The affected area is the front of the torso, arm, head or neck, back of the torso and leg; the photograph was taken at a distance; the patient is 18–29, female:
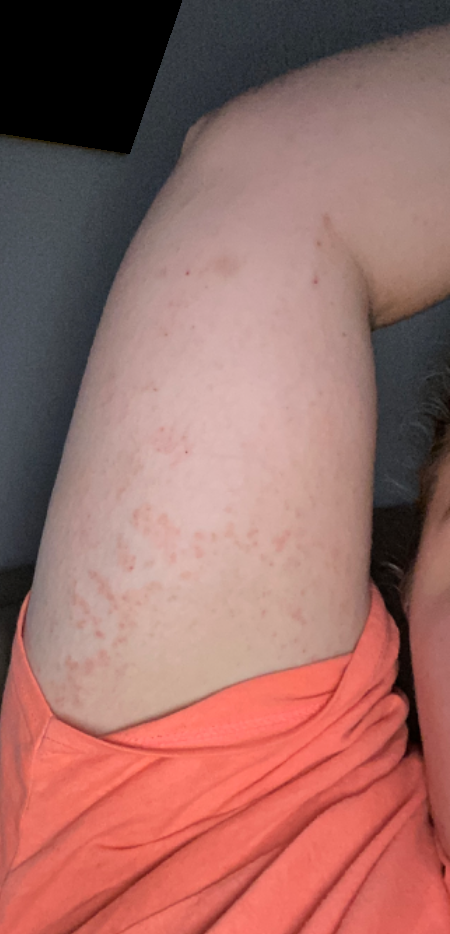diagnostic considerations: Contact dermatitis, NOS (0.55); Eczema (0.27); Keratosis pilaris (0.18).